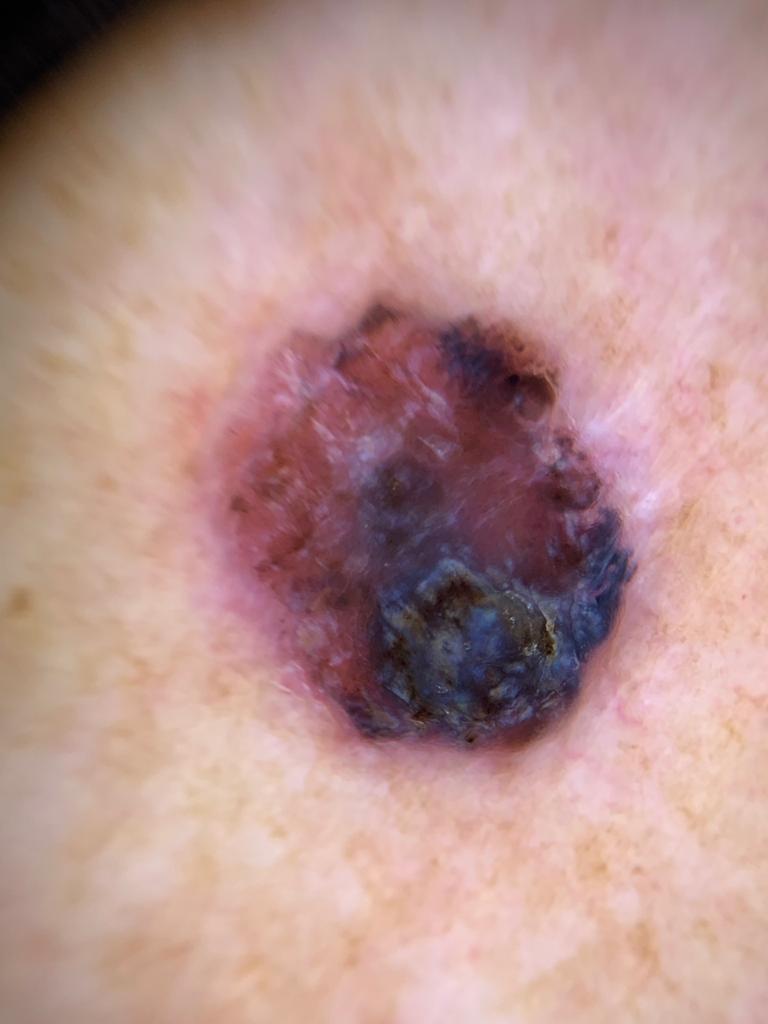lesion_location:
  region: the trunk
  detail: the posterior trunk
diagnosis:
  name: Melanoma
  malignancy: malignant
  confirmation: histopathology